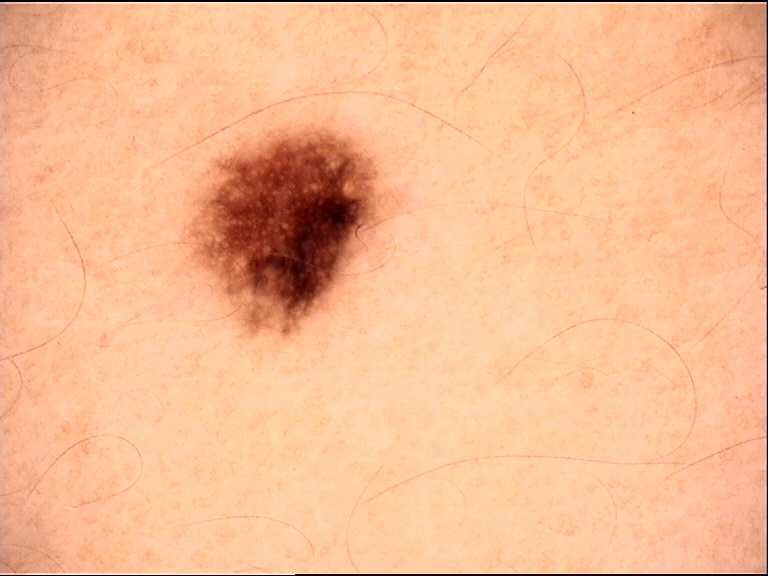diagnosis:
  name: dysplastic junctional nevus
  code: jd
  malignancy: benign
  super_class: melanocytic
  confirmation: expert consensus